A dermoscopic image of a skin lesion: 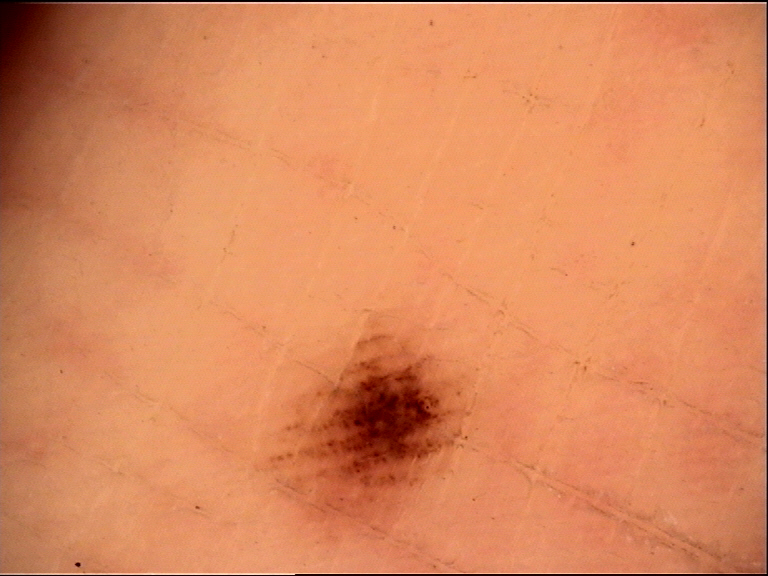Conclusion: The diagnosis was a benign lesion — an acral dysplastic junctional nevus.